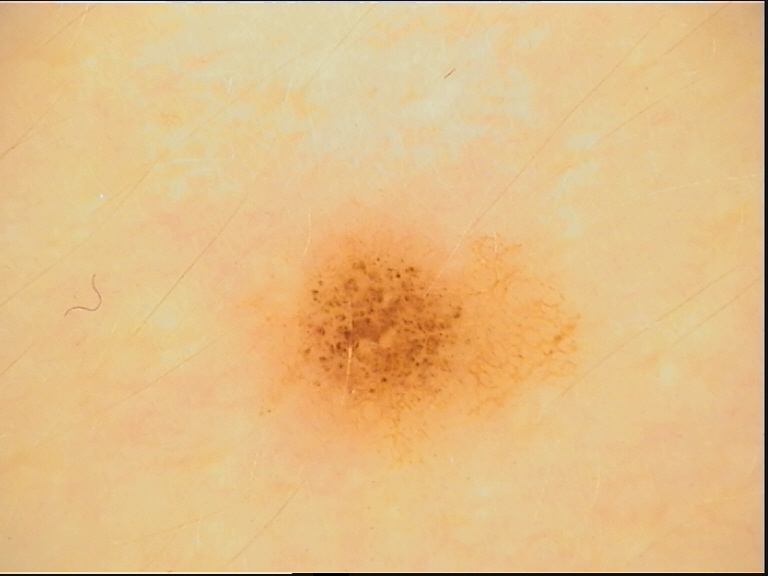label: acral dysplastic junctional nevus (expert consensus).